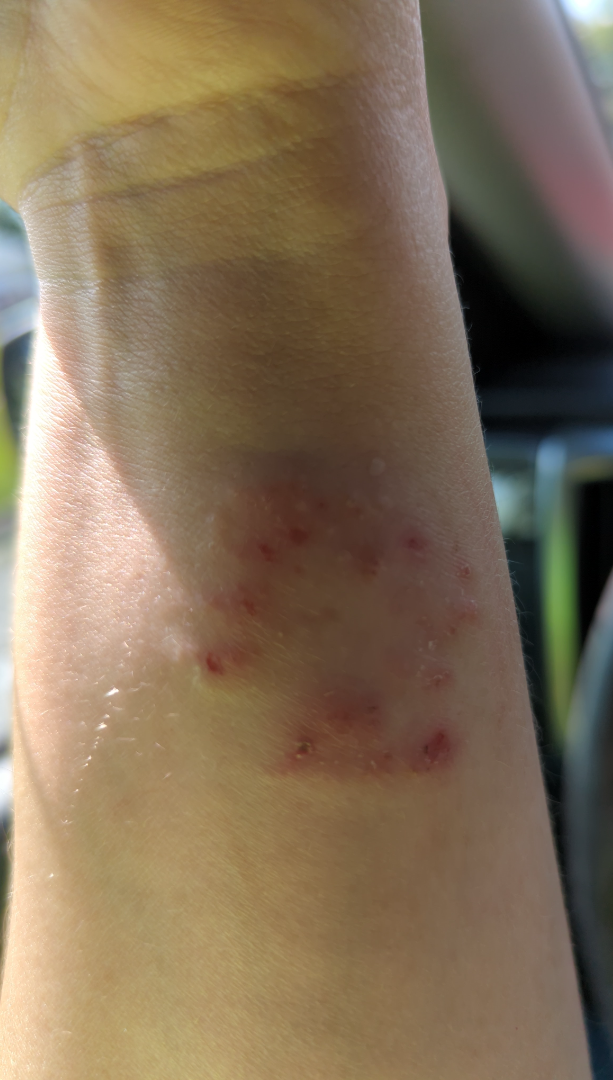{
  "patient": "female, age 30–39",
  "shot_type": "close-up",
  "body_site": [
    "arm",
    "head or neck",
    "leg",
    "front of the torso"
  ],
  "differential": "Allergic Contact Dermatitis"
}